A dermoscopic close-up of a skin lesion.
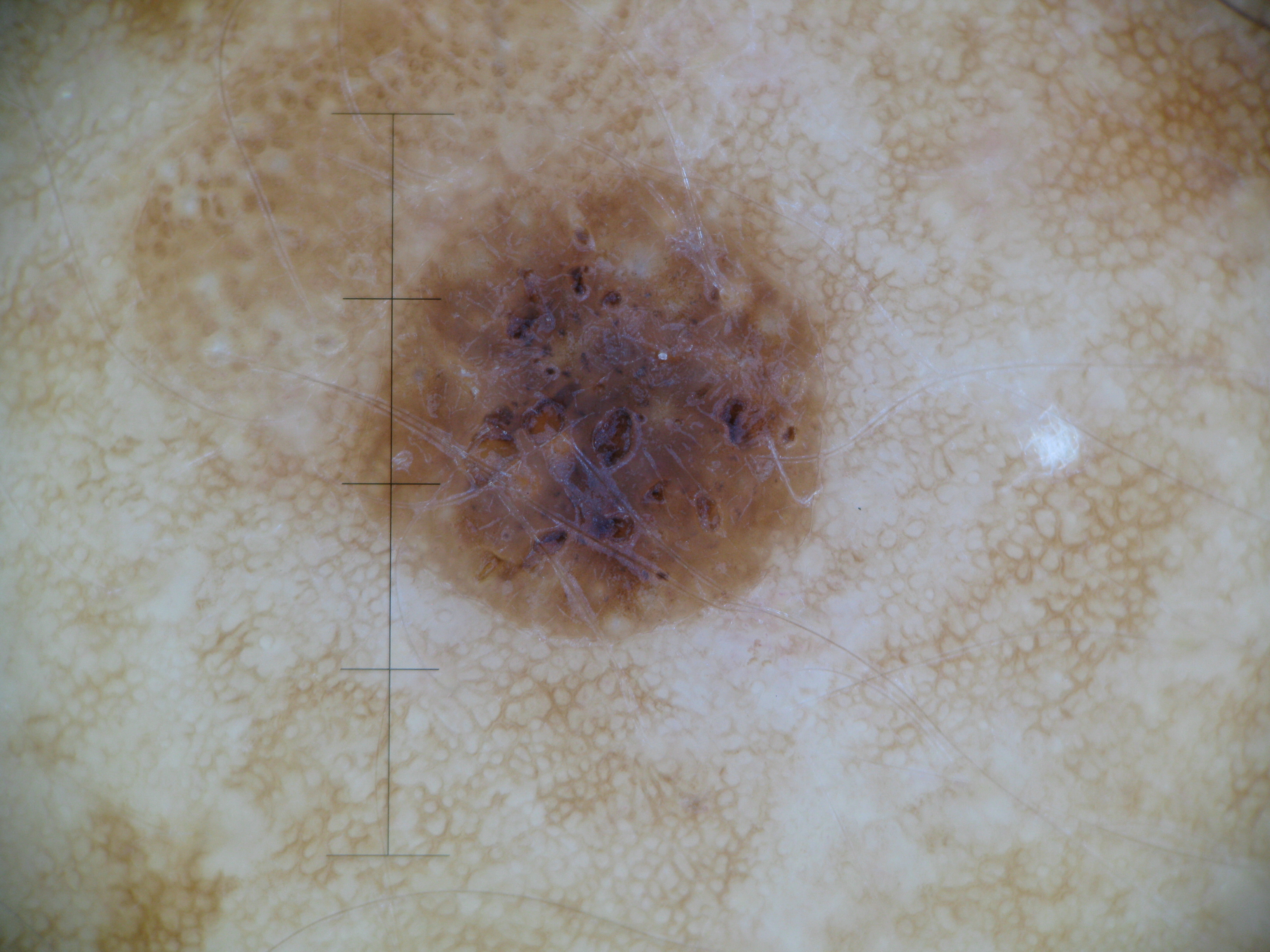label — seborrheic keratosis (expert consensus).